Located on the leg. Close-up view. The subject is 30–39, female.
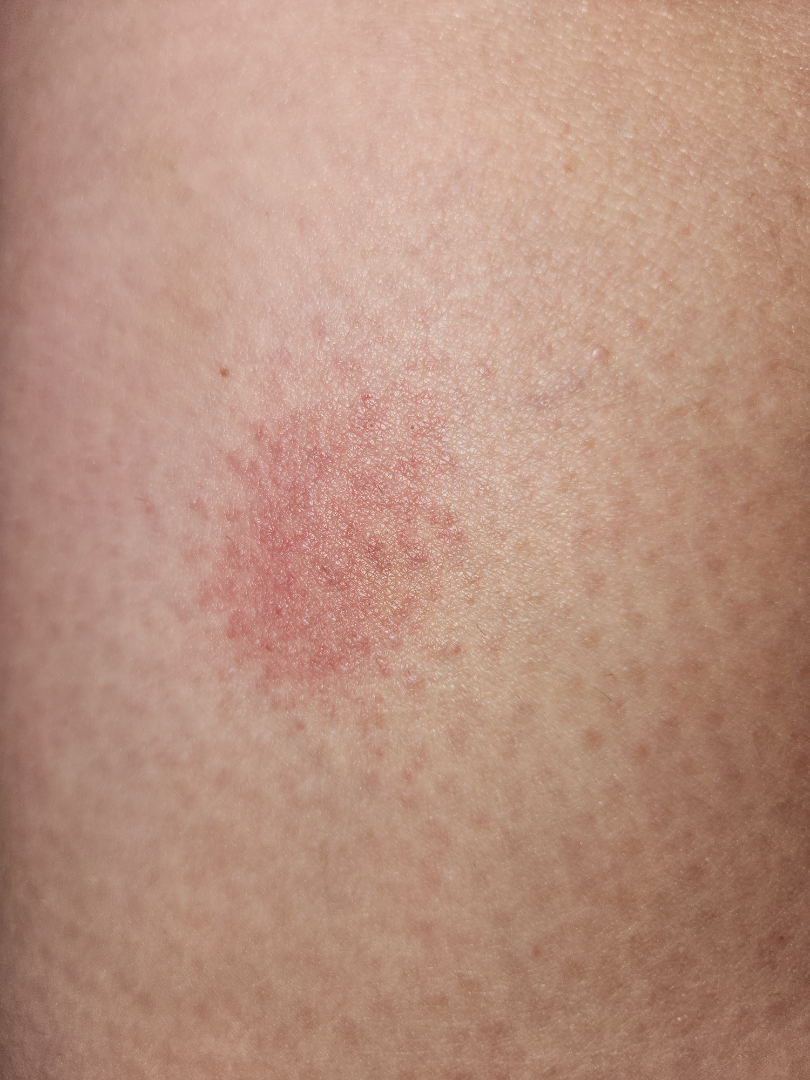On photographic review: the differential is split between Pigmented purpuric eruption, Drug Rash and Eczema.